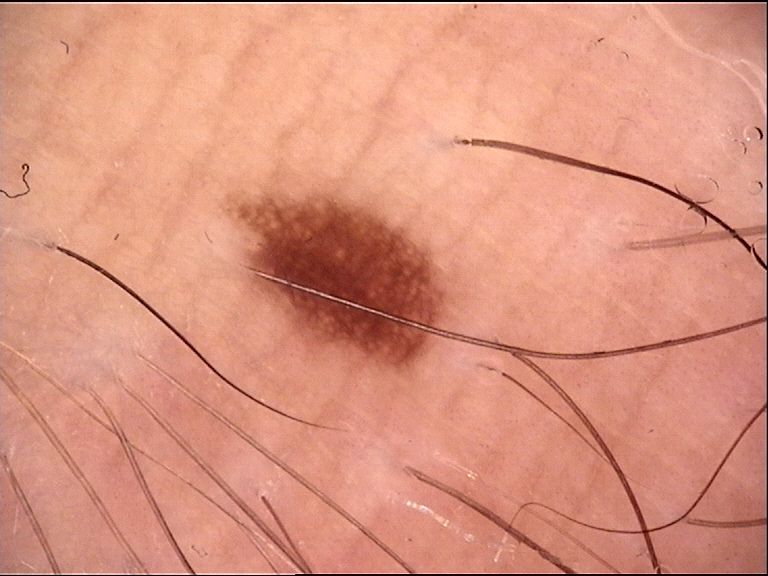image: dermoscopy | assessment: dysplastic junctional nevus (expert consensus).